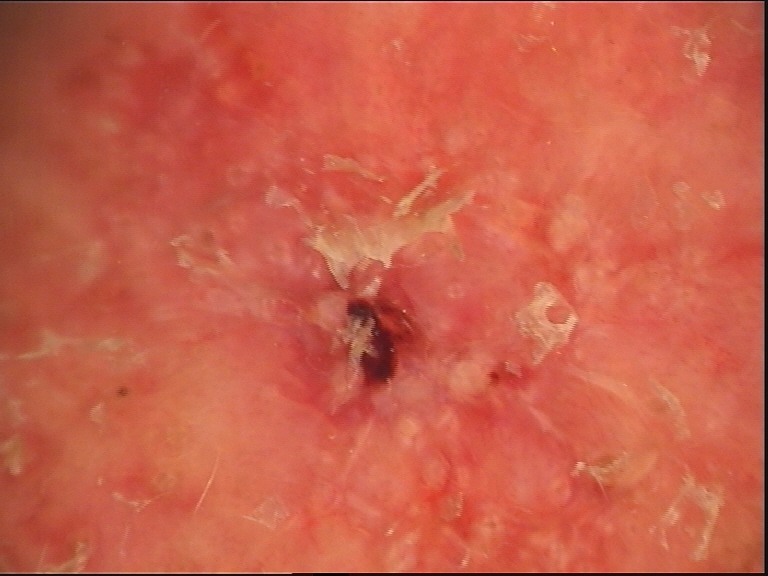modality: dermoscopy, subtype: keratinocytic, pathology: basal cell carcinoma (biopsy-proven).